A skin lesion imaged with a dermatoscope.
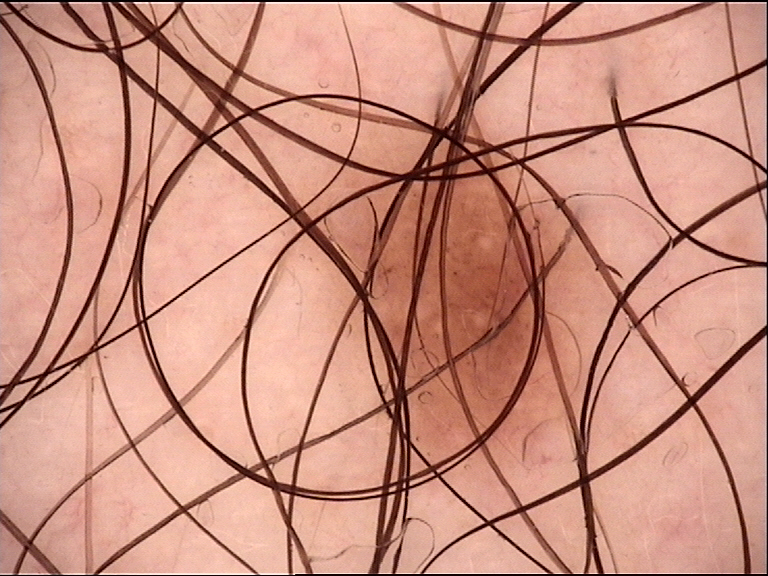Impression: The diagnostic label was a dysplastic junctional nevus.